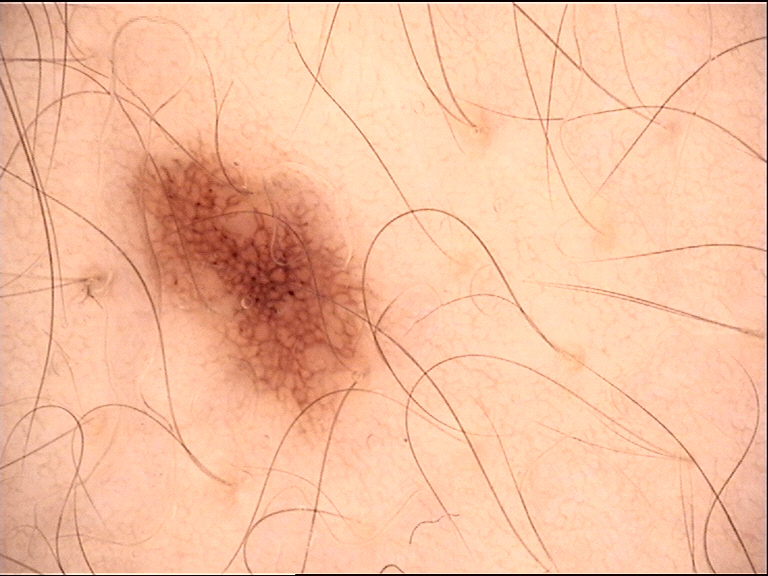Case:
* imaging: dermoscopy
* diagnosis: dysplastic junctional nevus (expert consensus)